A dermoscopy image of a single skin lesion; a female patient approximately 85 years of age or older: 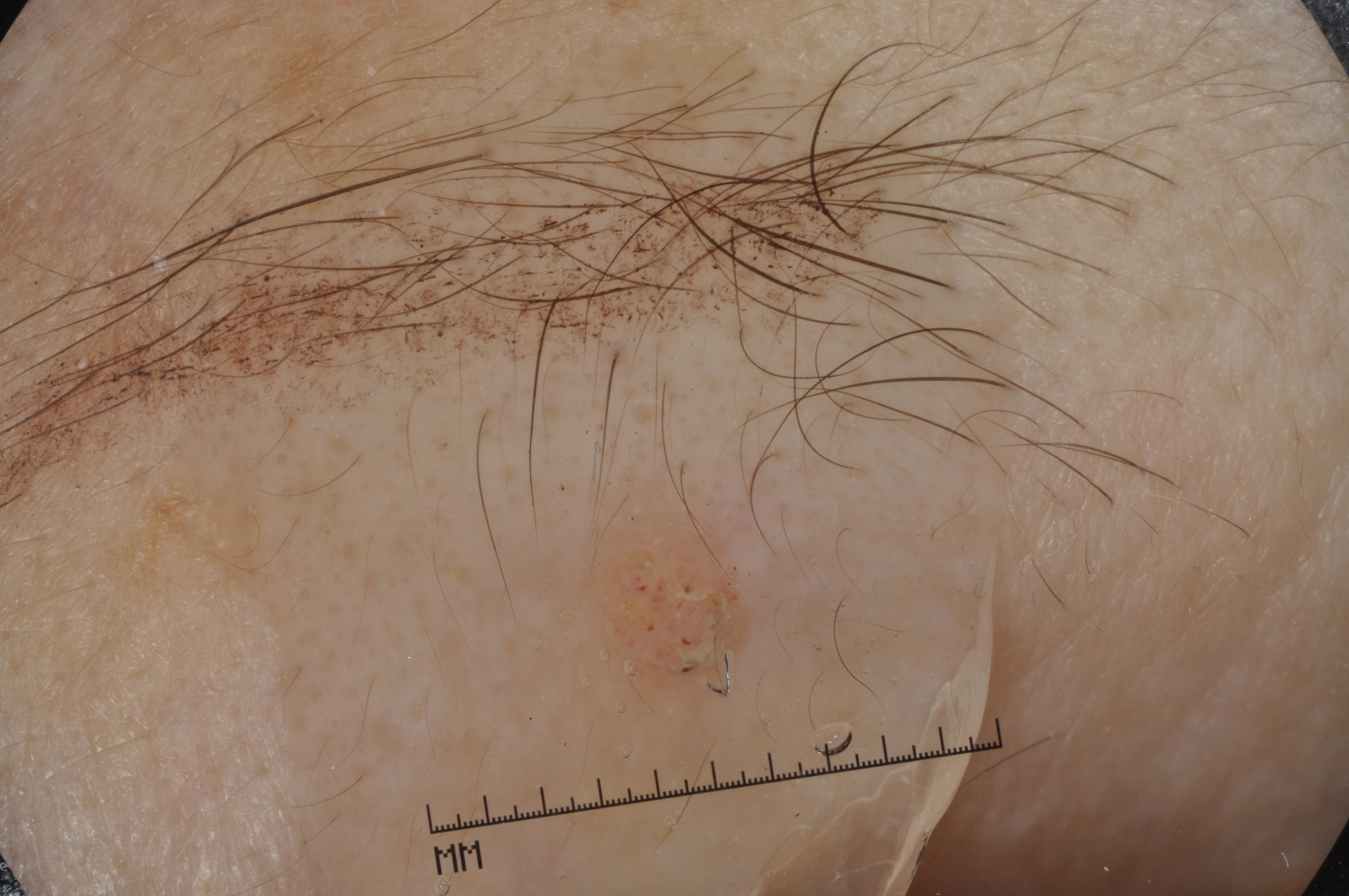Dermoscopic examination shows milia-like cysts; no pigment network, streaks, or negative network.
A small lesion within a wider field of skin.
With coordinates (x1, y1, x2, y2), the visible lesion spans 581, 483, 755, 710.
The clinical diagnosis was a seborrheic keratosis.